A dermoscopy image of a single skin lesion.
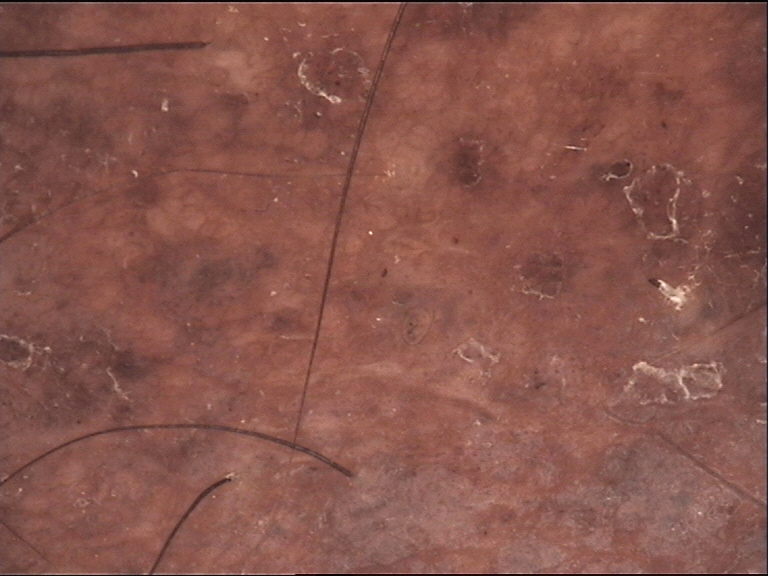classification: banal, diagnostic label: congenital compound nevus (expert consensus).